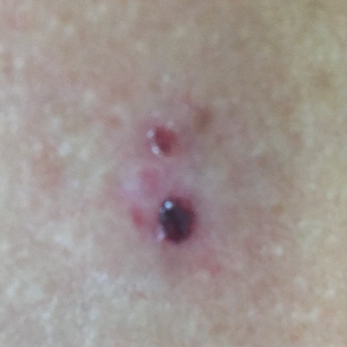On biopsy, the diagnosis was a basal cell carcinoma.